A dermoscopic image of a skin lesion.
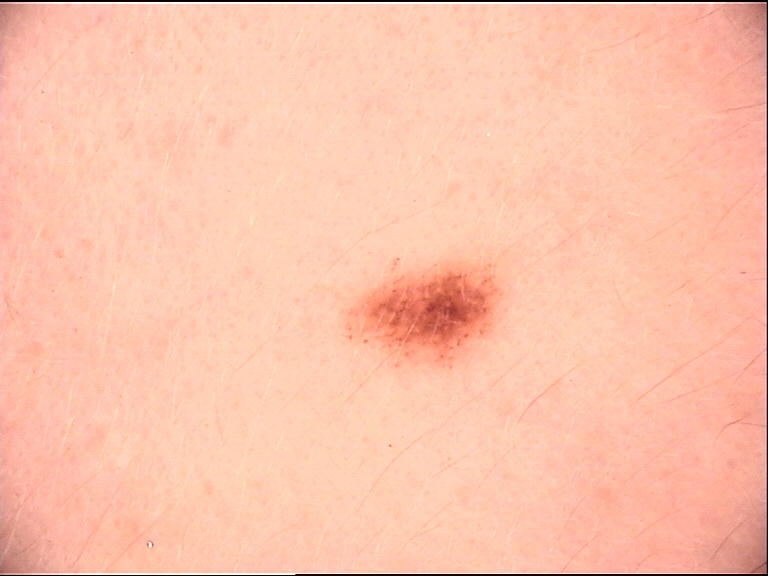The diagnosis was a banal lesion — a Miescher nevus.